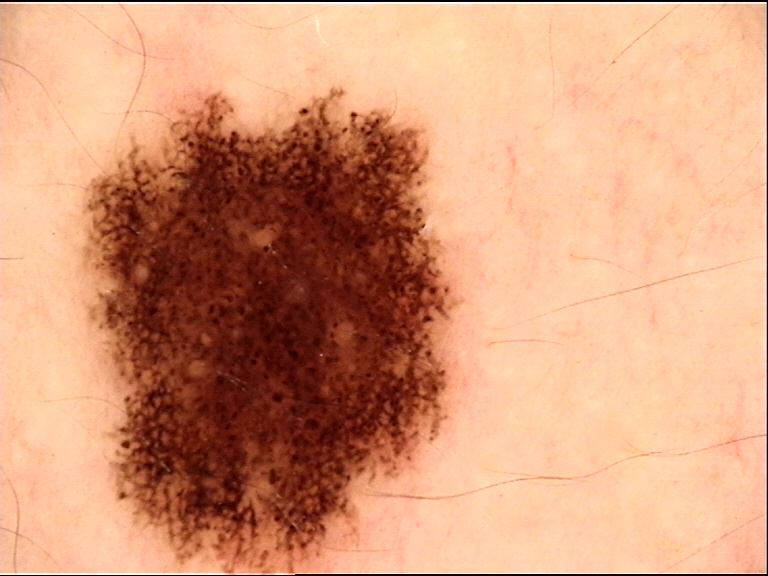A dermoscopic photograph of a skin lesion.
Classified as a dysplastic compound nevus.